A clinical close-up of a skin lesion. A male subject 77 years of age. Collected as part of a research study, without a referral diagnosis: 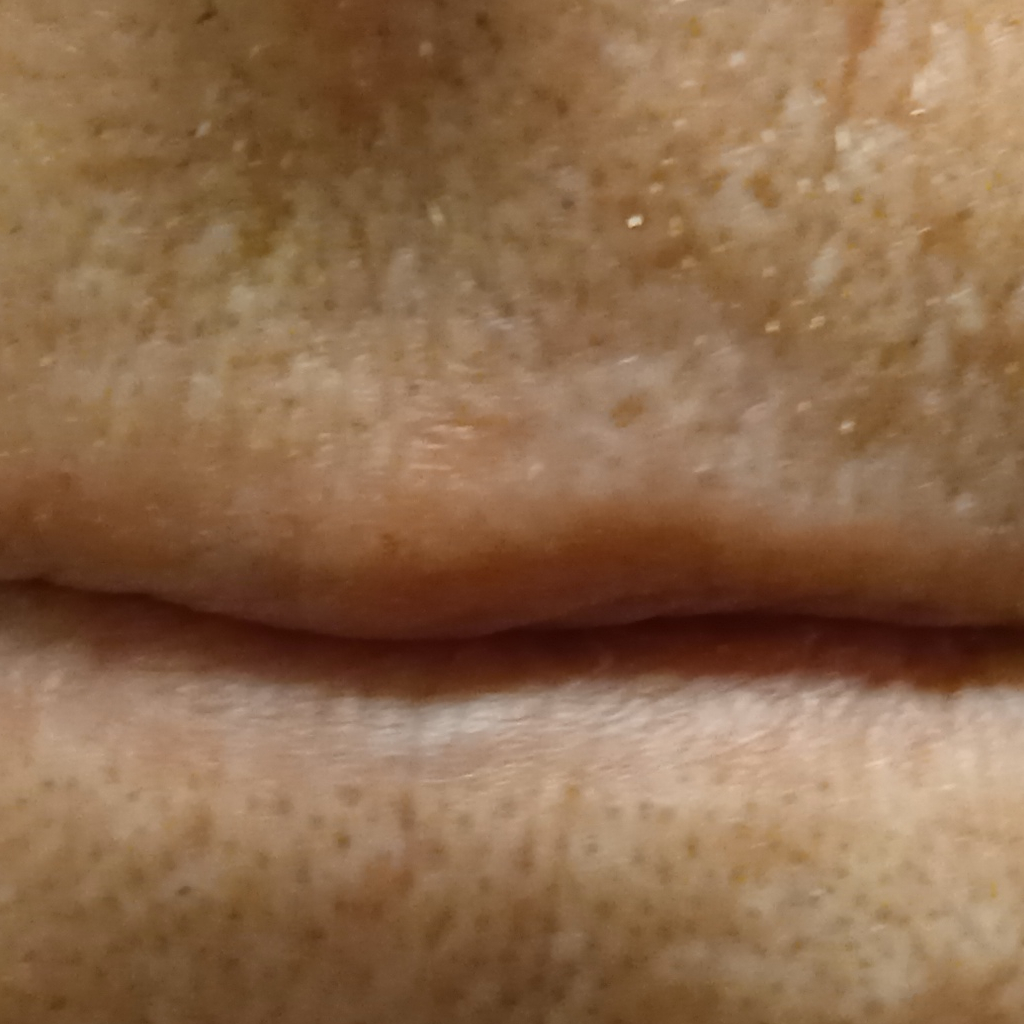The lesion is located on the face.
The lesion measures approximately 6.4 mm.
The diagnostic impression was an actinic keratosis.